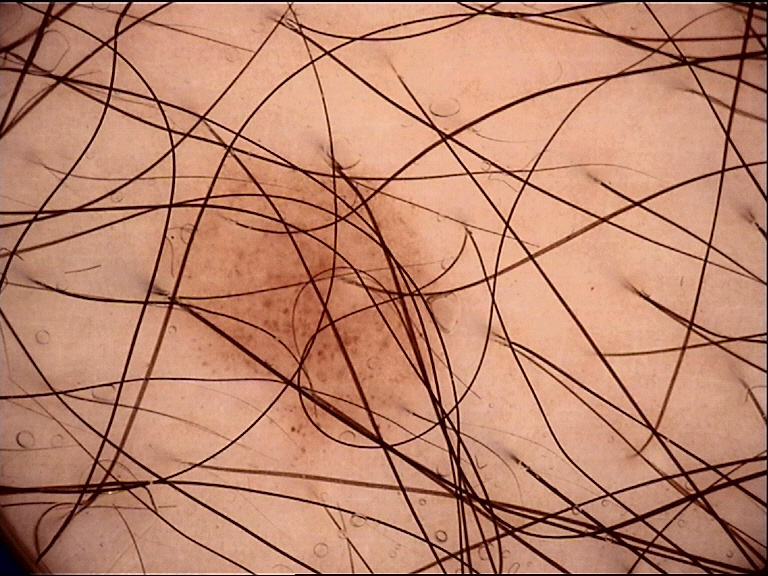The diagnosis was a benign lesion — a dysplastic junctional nevus.